Close-up view.
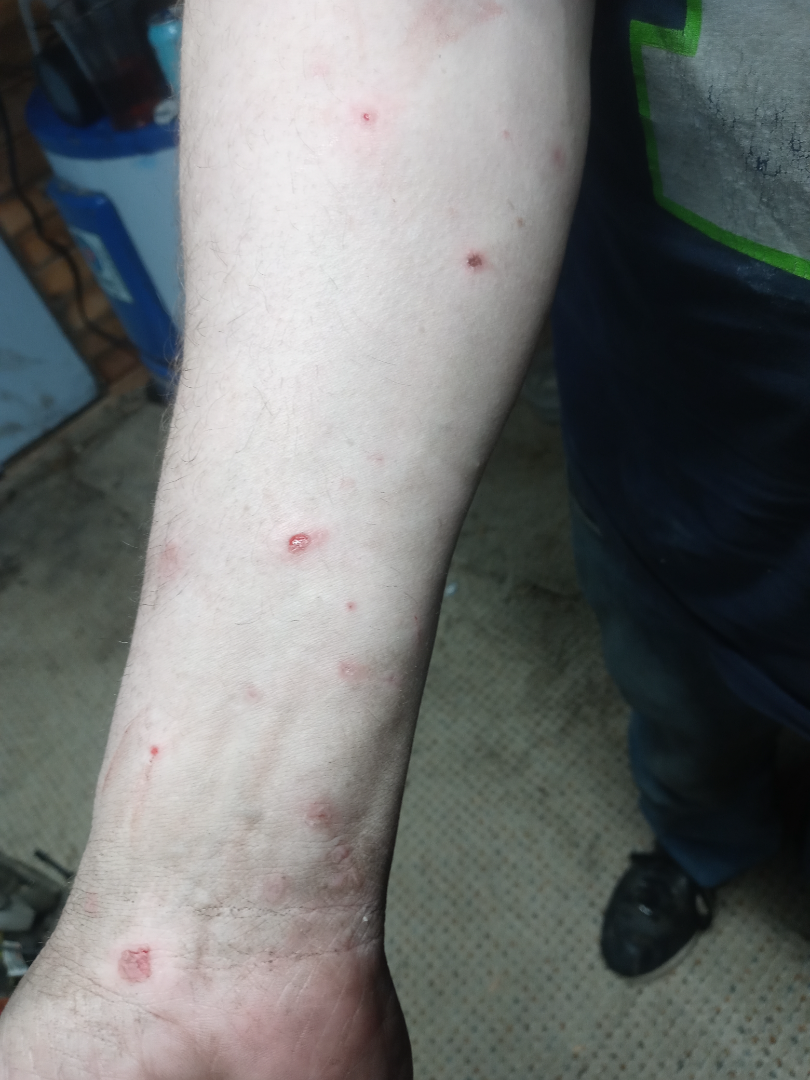On remote dermatologist review: the differential, in no particular order, includes Impetigo and Insect Bite; a more distant consideration is Eczema.